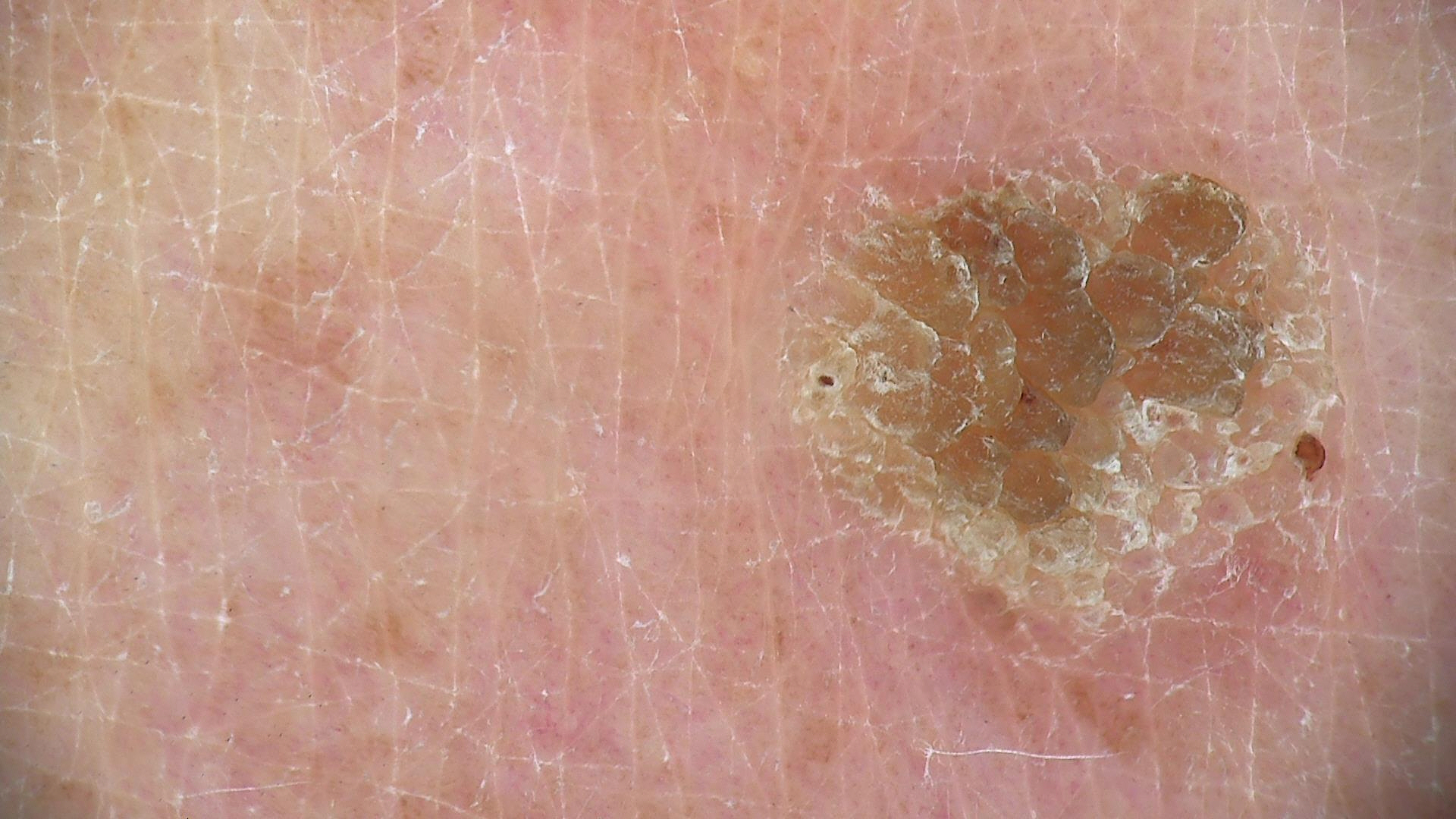This is a keratinocytic lesion. Labeled as a benign lesion — a seborrheic keratosis.